A dermatoscopic image of a skin lesion, a male subject approximately 35 years of age — 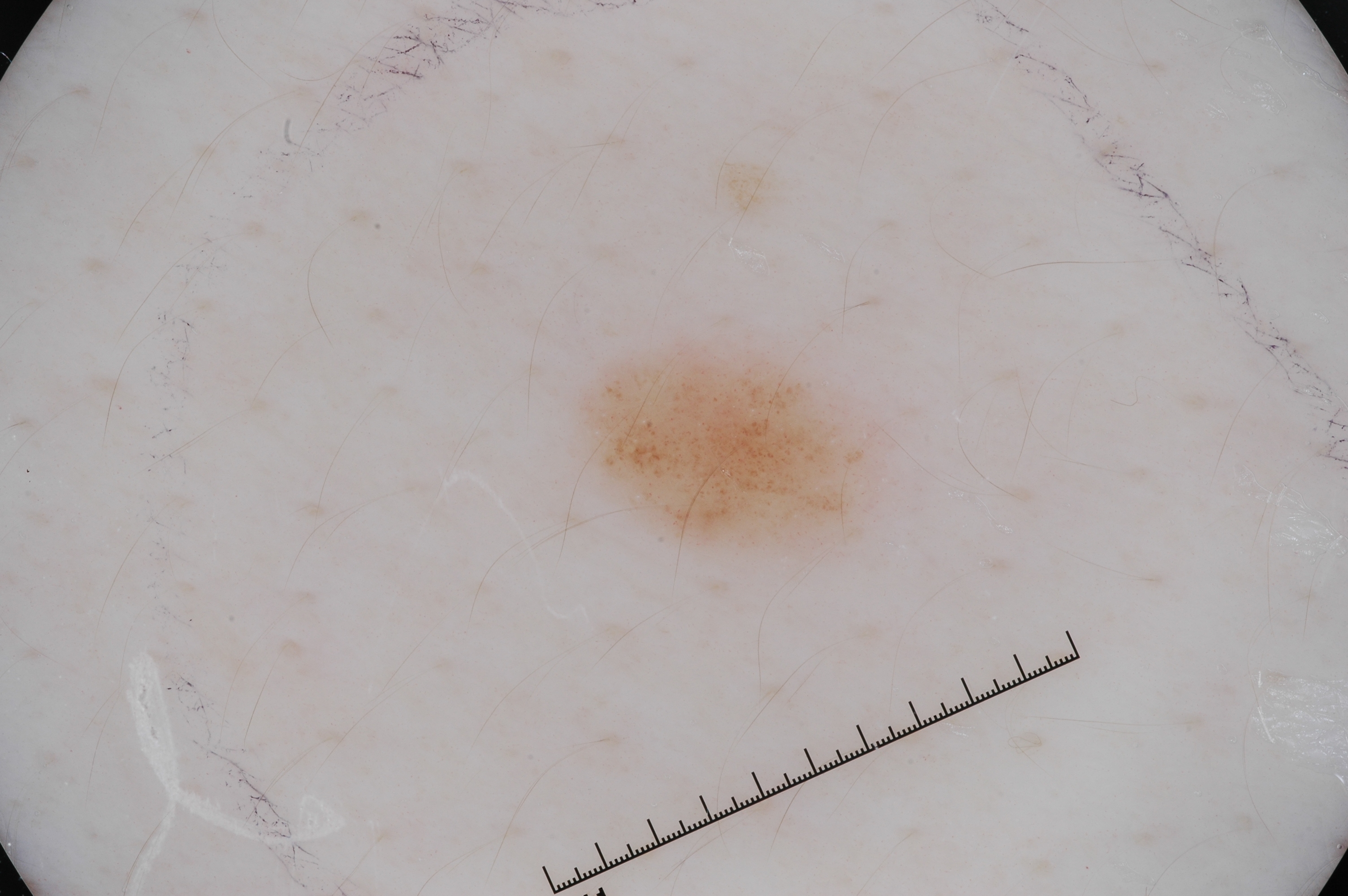dermoscopic findings = milia-like cysts | location = bbox=[590, 343, 874, 553] | lesion extent = small | diagnosis = a melanocytic nevus, a benign skin lesion.